A skin lesion imaged with a dermatoscope.
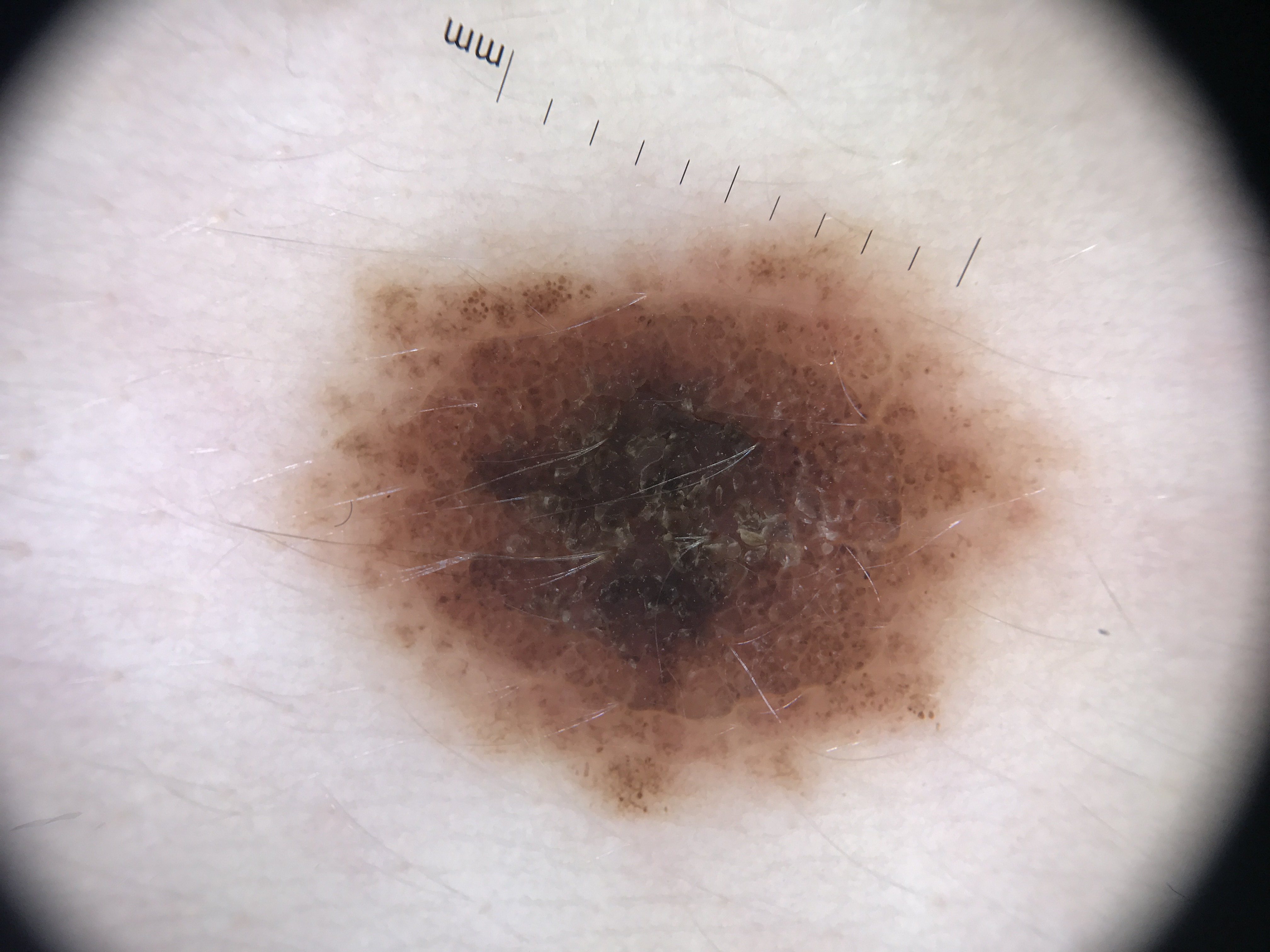{
  "diagnosis": {
    "name": "dysplastic compound nevus",
    "code": "cd",
    "malignancy": "benign",
    "super_class": "melanocytic",
    "confirmation": "expert consensus"
  }
}